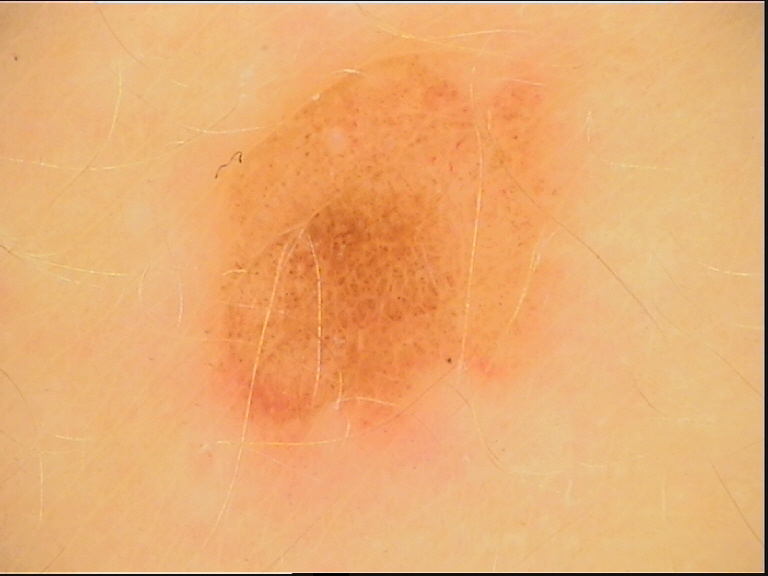modality=dermatoscopy; diagnosis=dysplastic junctional nevus (expert consensus).